A dermatoscopic image of a skin lesion; recorded as Fitzpatrick III; a male subject approximately 40 years of age; the chart records a first-degree relative with melanoma.
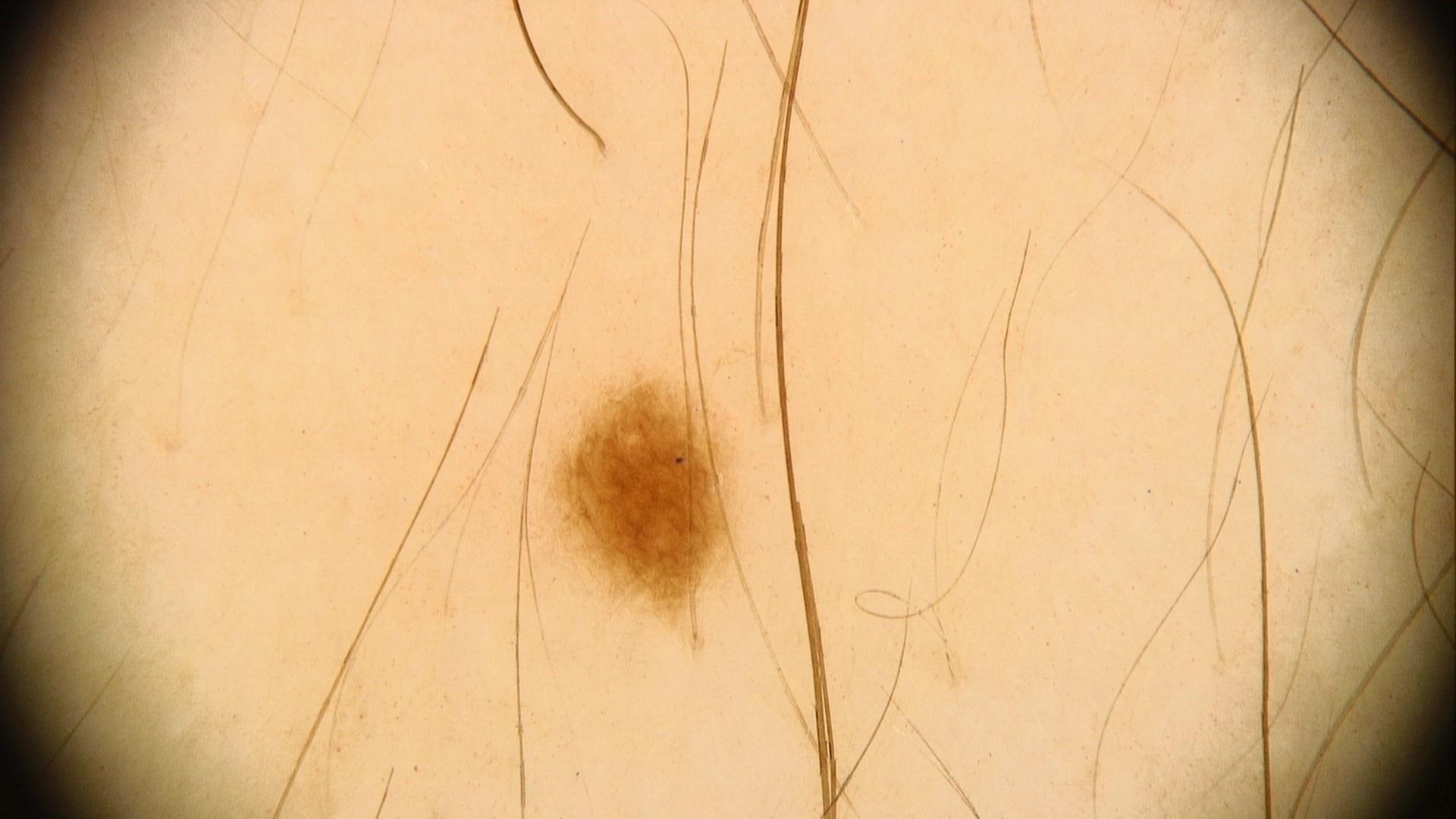Case:
- body site — the trunk (the anterior trunk)
- assessment — Nevus